The patient was assessed as Fitzpatrick phototype II · history notes prior malignancy (patient or family) and prior skin cancer (patient or family) · a clinical close-up photograph of a skin lesion: 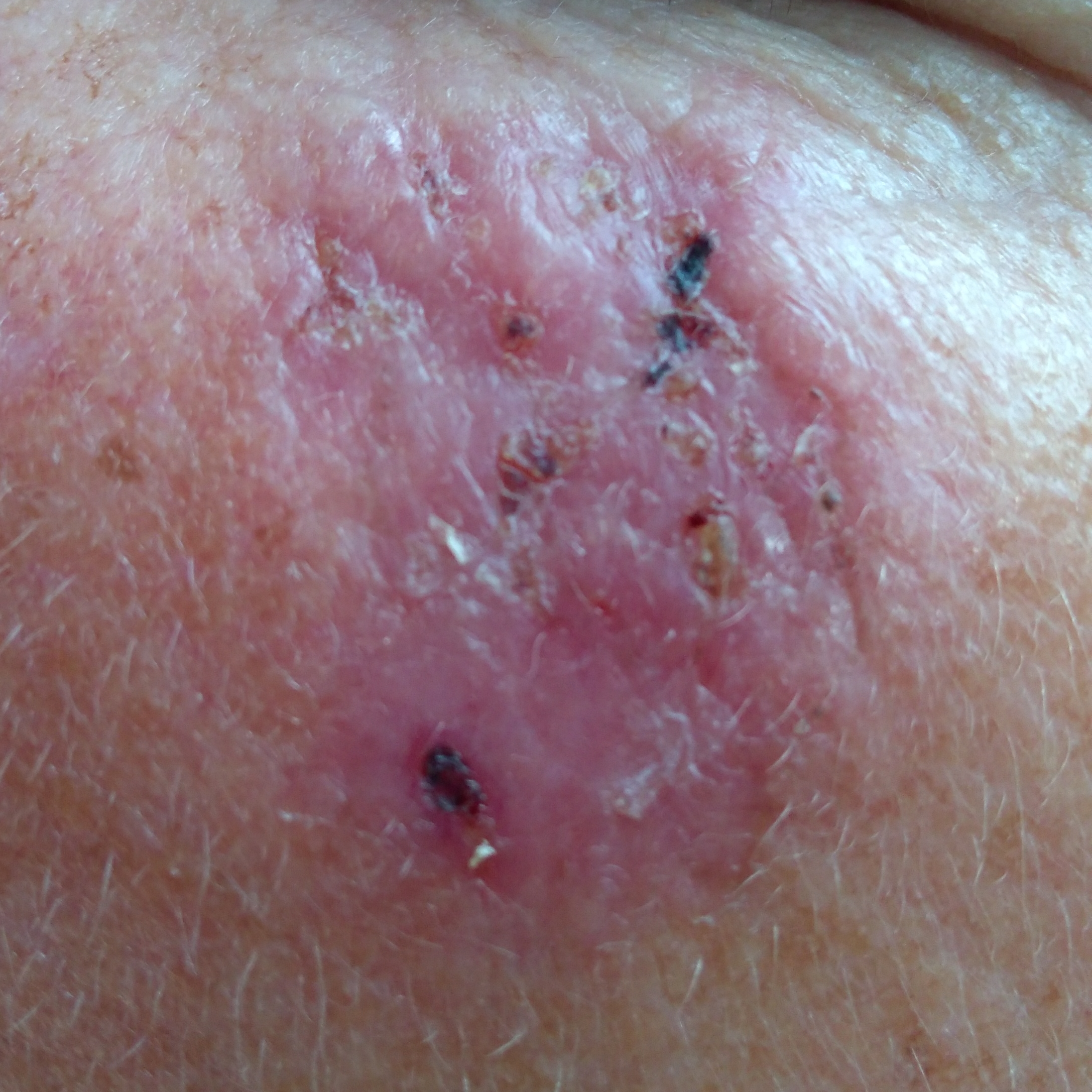Q: Lesion size?
A: 30 × 25 mm
Q: What symptoms does the patient report?
A: bleeding, elevation, itching
Q: What is the diagnosis?
A: basal cell carcinoma (biopsy-proven)